A skin lesion imaged with a dermatoscope.
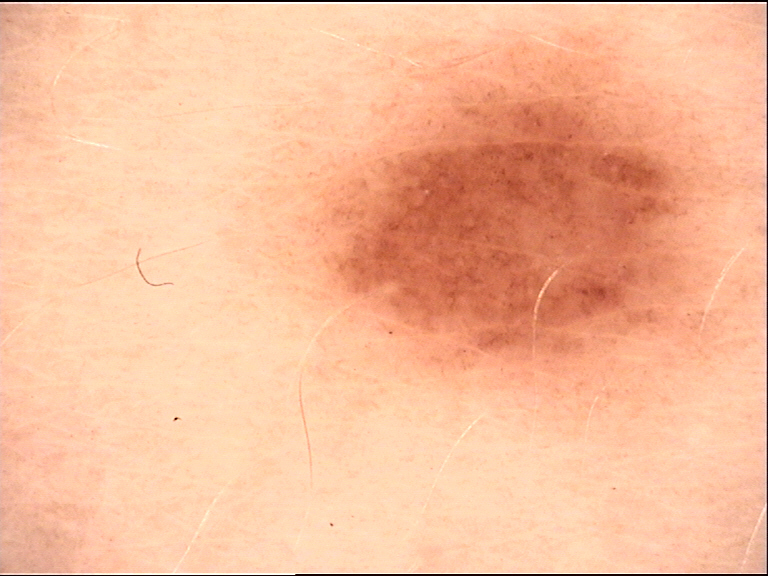Conclusion: Labeled as a dysplastic junctional nevus.